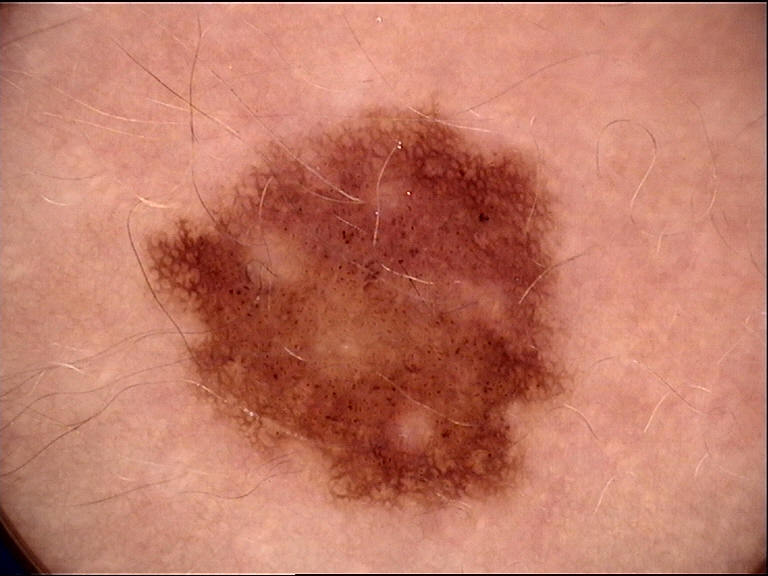Dermoscopy of a skin lesion. Classified as a benign lesion — a dysplastic junctional nevus.